The photograph is a close-up of the affected area · the patient is a male aged 30–39 · the affected area is the back of the torso and front of the torso.
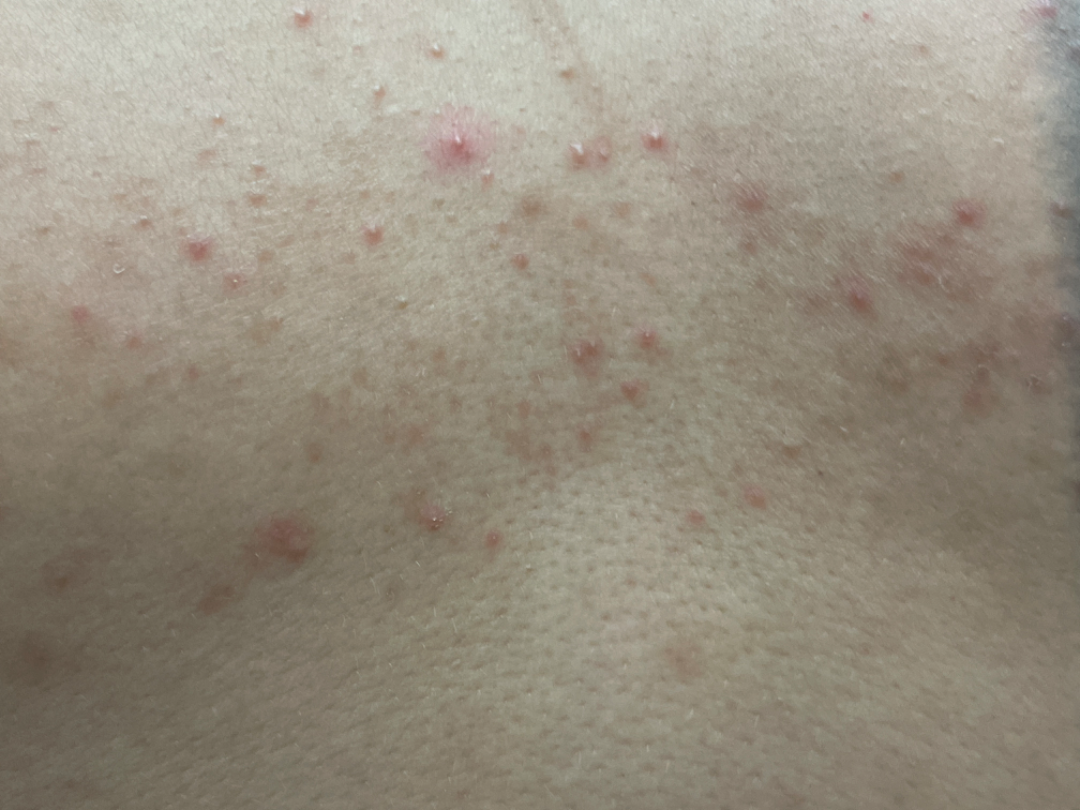No associated systemic symptoms reported.
Self-categorized by the patient as a rash.
On photographic review, Folliculitis (56%); Acne (33%); Grover's disease (11%).